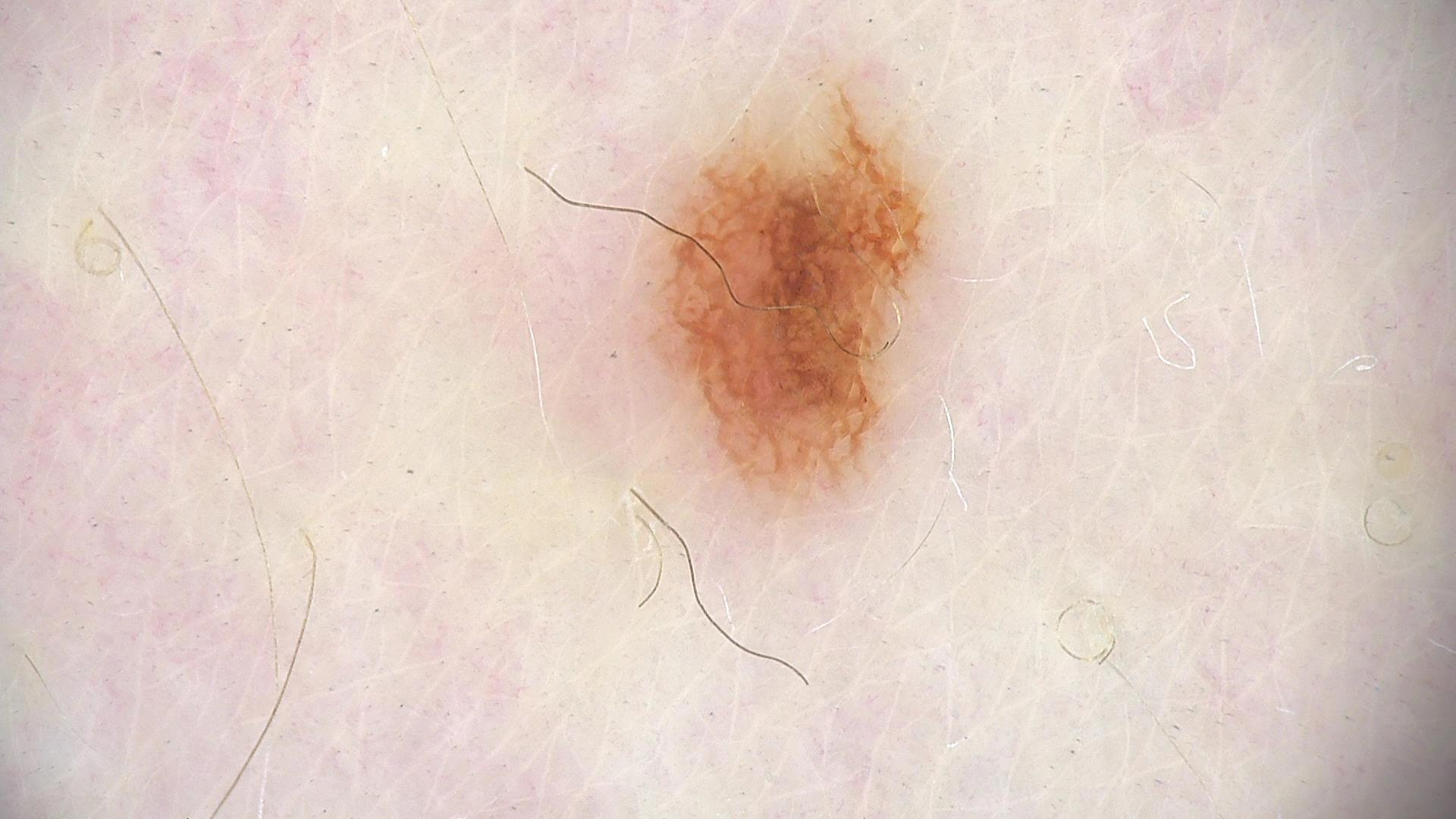imaging = dermatoscopy | diagnostic label = dysplastic junctional nevus (expert consensus).